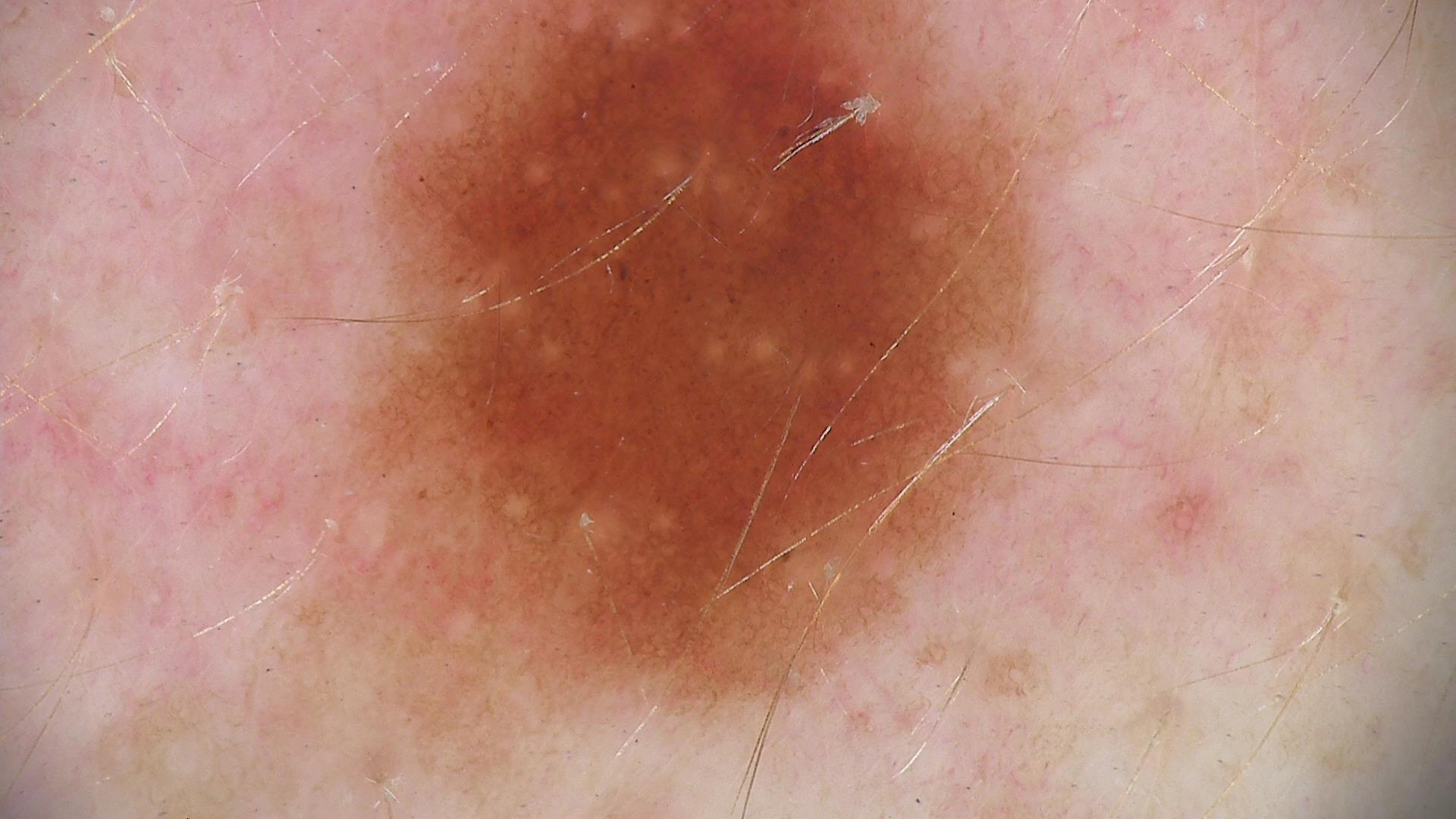A dermoscopy image of a single skin lesion. The diagnosis was a dysplastic junctional nevus.